A dermoscopic close-up of a skin lesion.
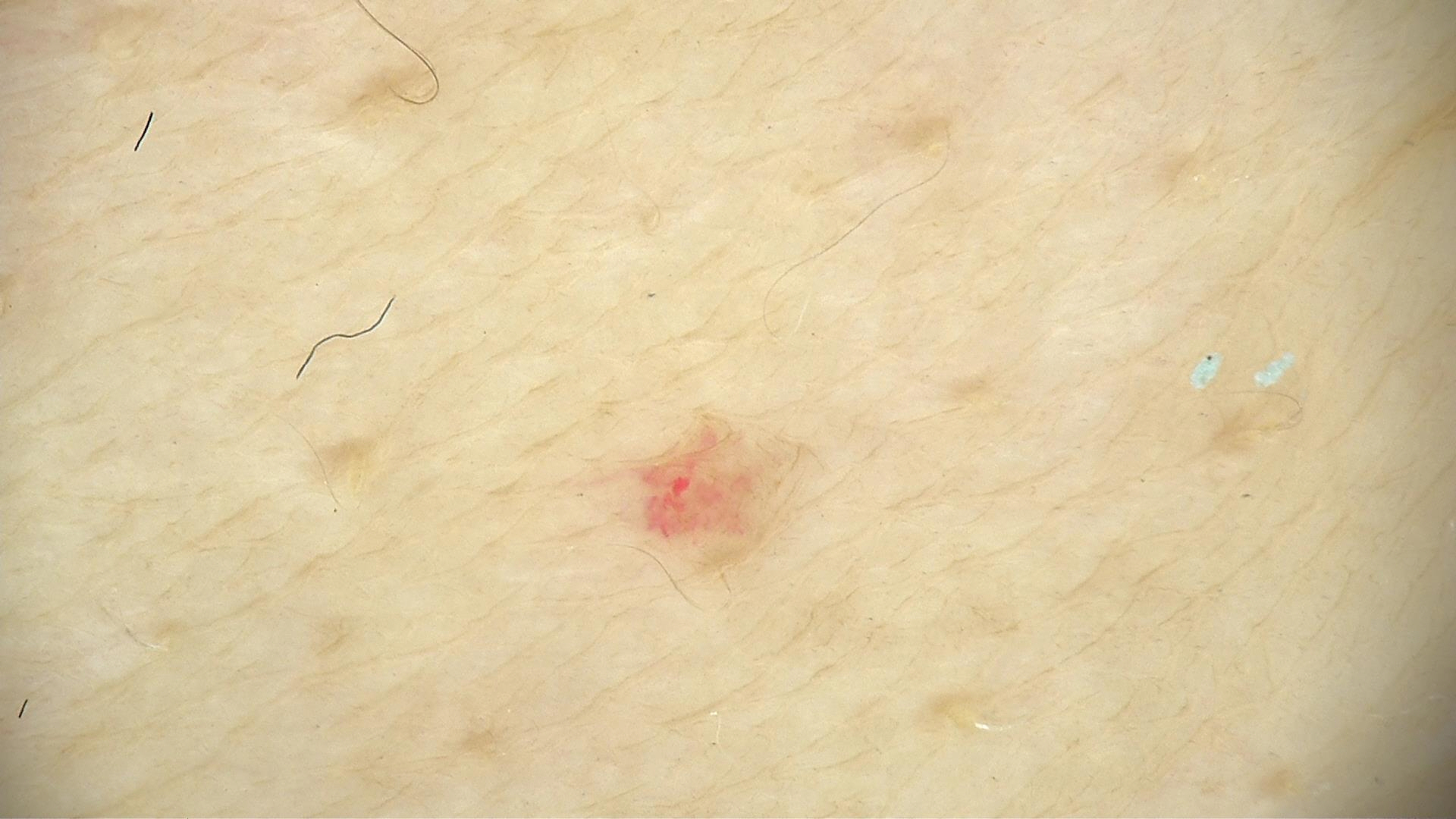classification: vascular, diagnosis: hemangioma (expert consensus).